A patient 10 years of age · a clinical photograph of a skin lesion.
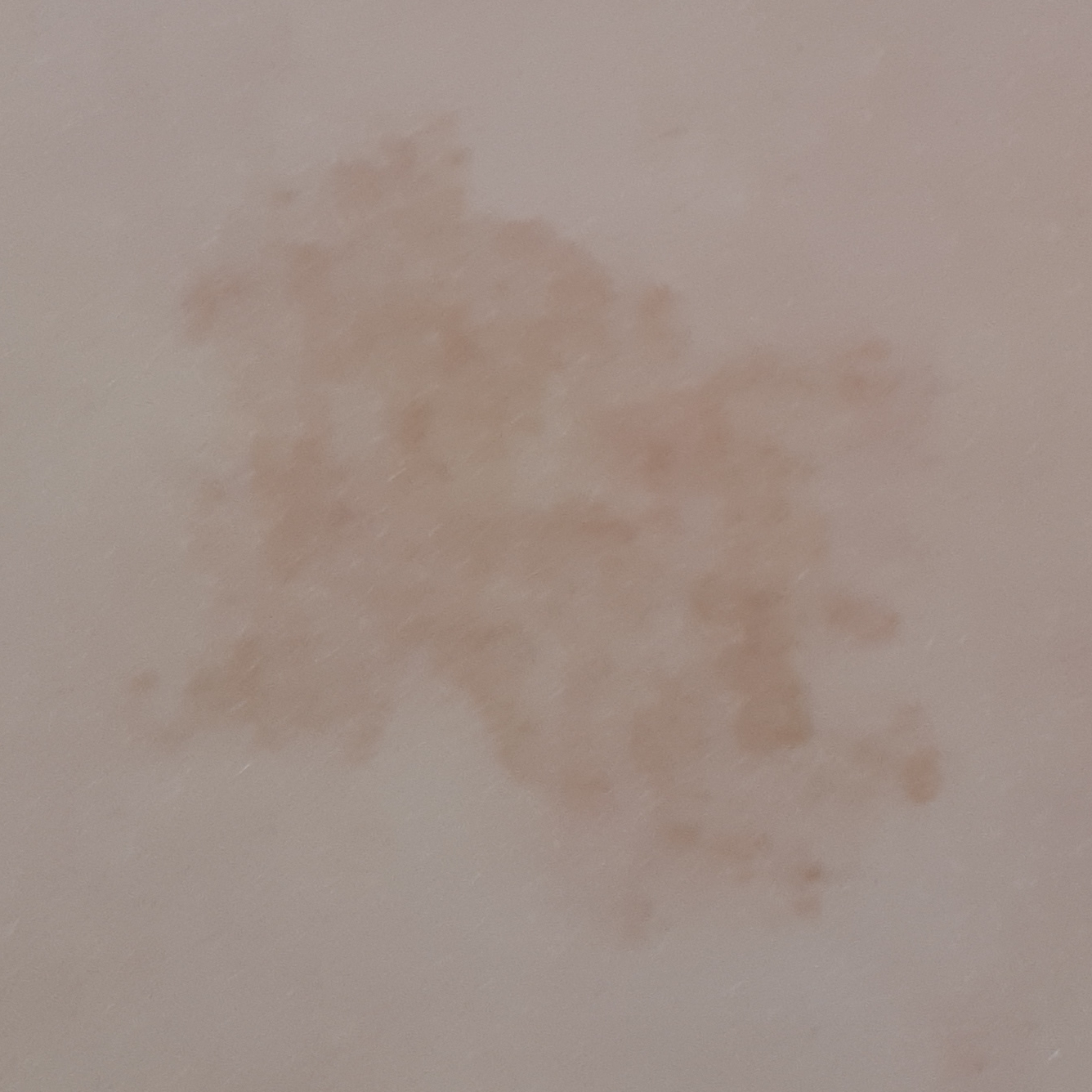The lesion is on the back. The patient reports that the lesion has changed and has grown, but has not bled. Clinically diagnosed as a nevus.